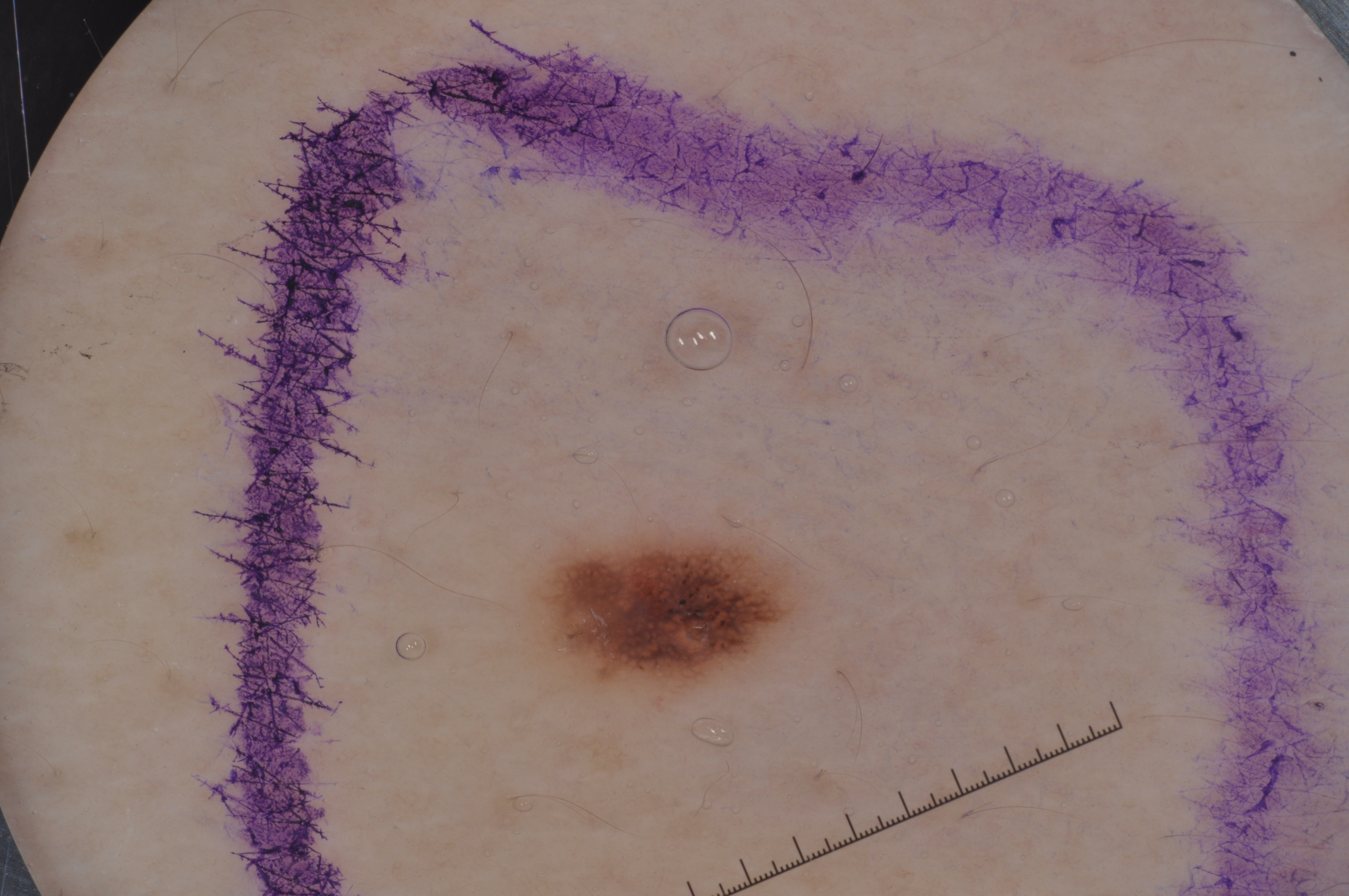subject=male, in their 40s | image type=dermoscopy of a skin lesion | lesion location=530 526 812 696 | lesion extent=~3% of the field | dermoscopic features=pigment network | diagnosis=a melanocytic nevus, a benign lesion.